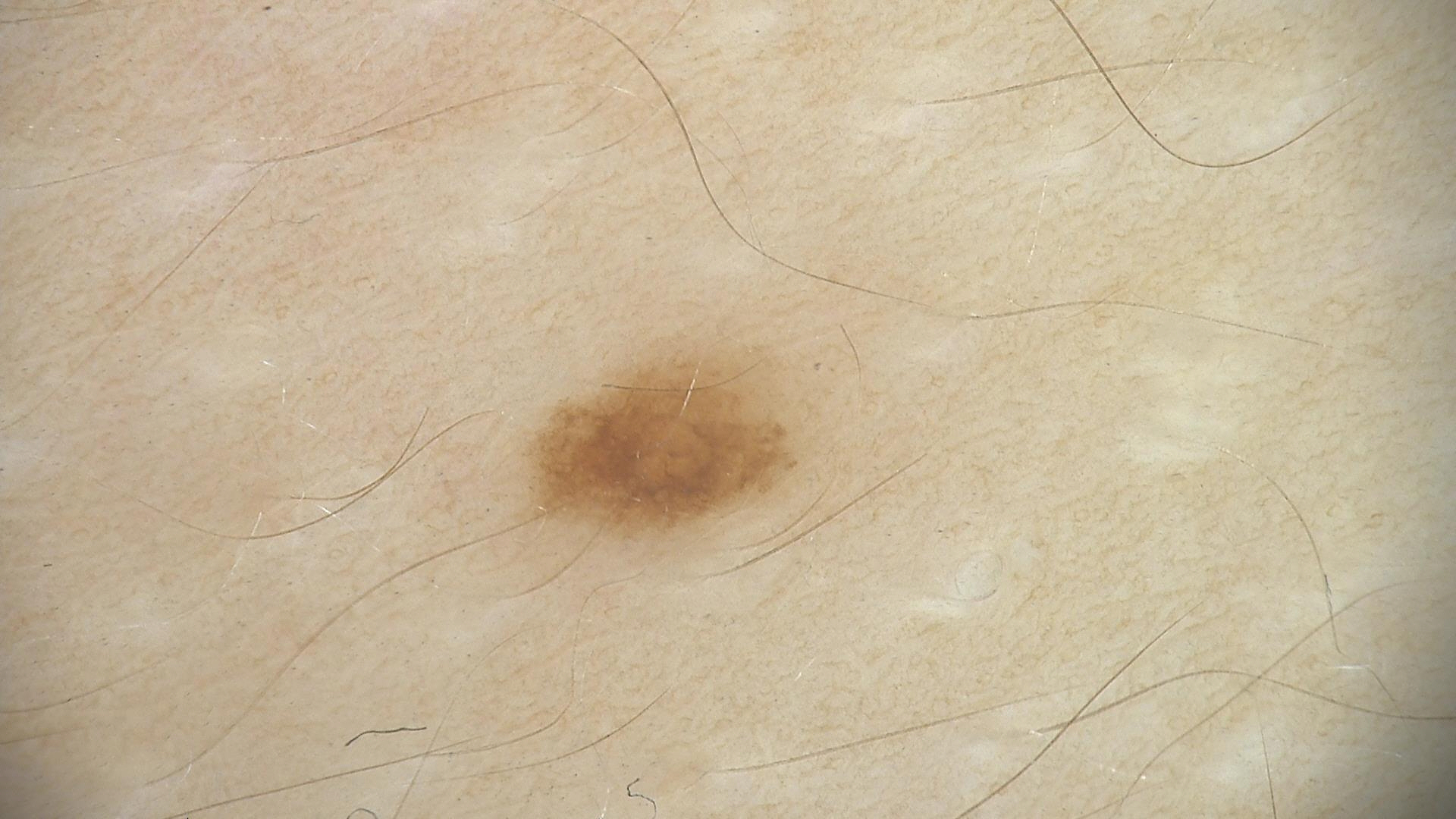Dermoscopy of a skin lesion. Classified as a dysplastic junctional nevus.